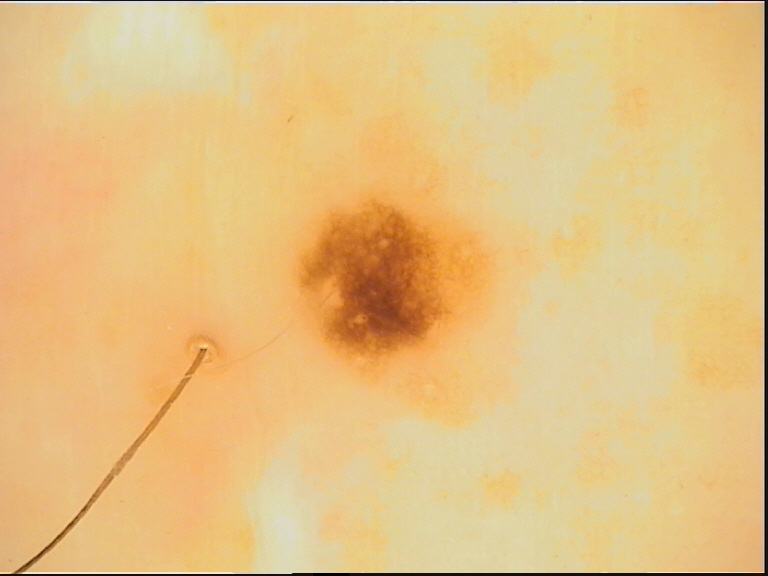Impression:
Classified as a dysplastic junctional nevus.